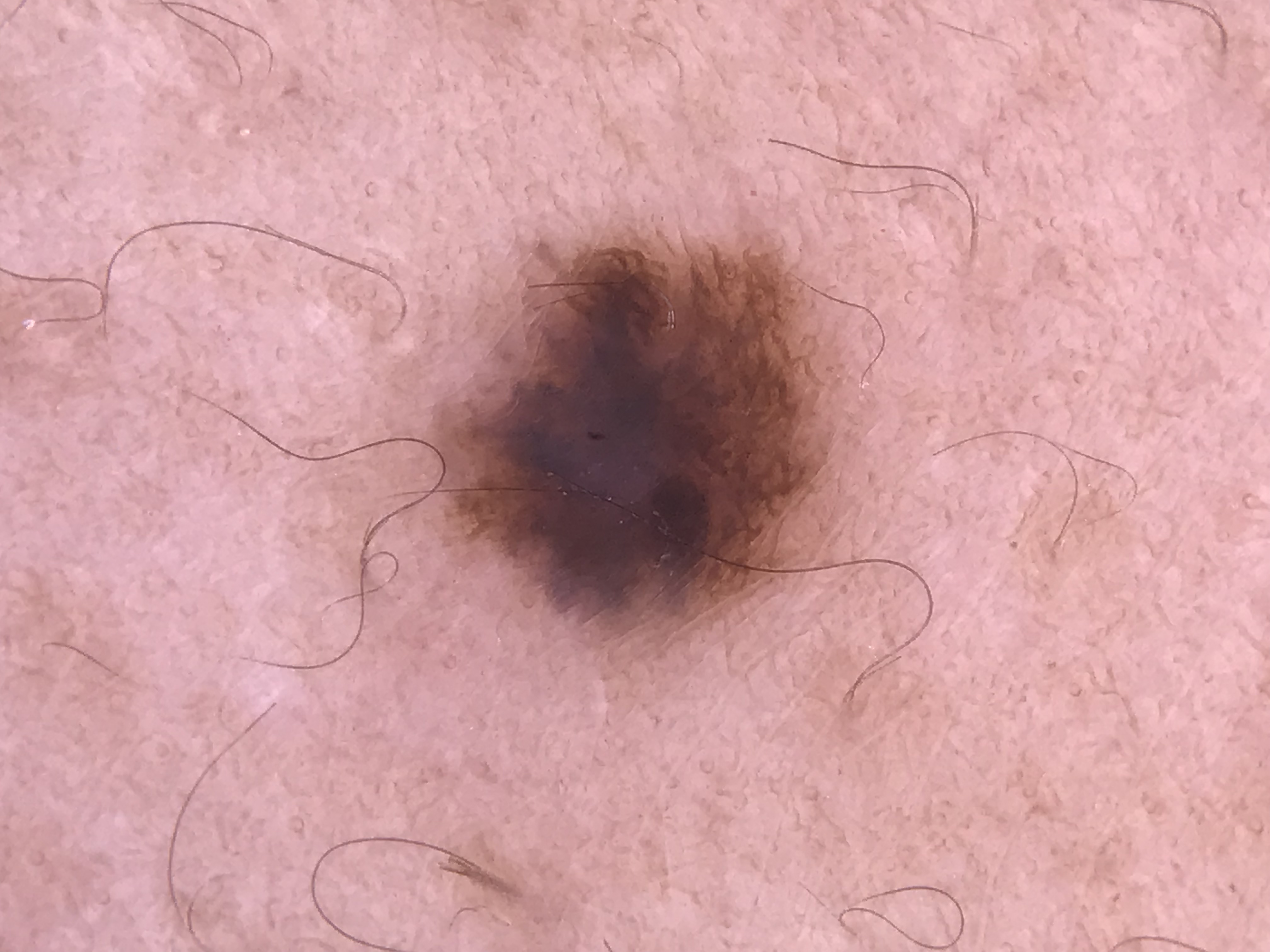Dermoscopy of a skin lesion. The diagnostic label was a dysplastic compound nevus.